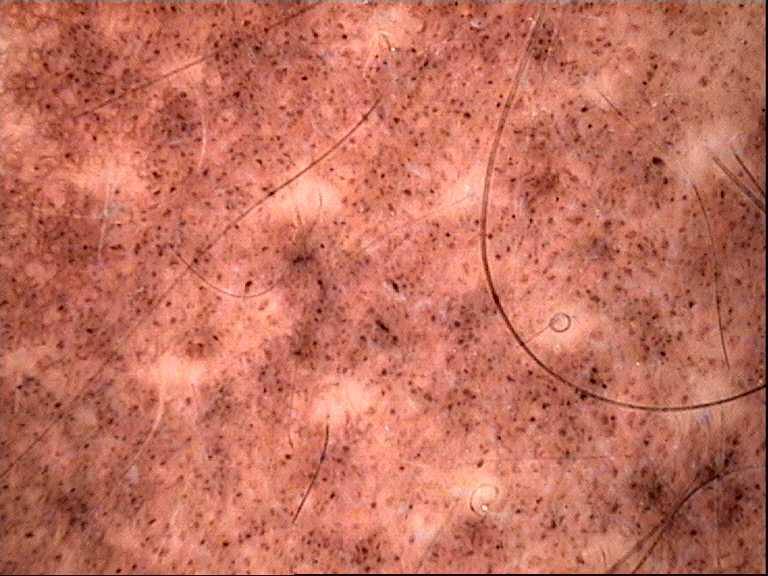imaging — dermatoscopy | class — congenital compound nevus (expert consensus).